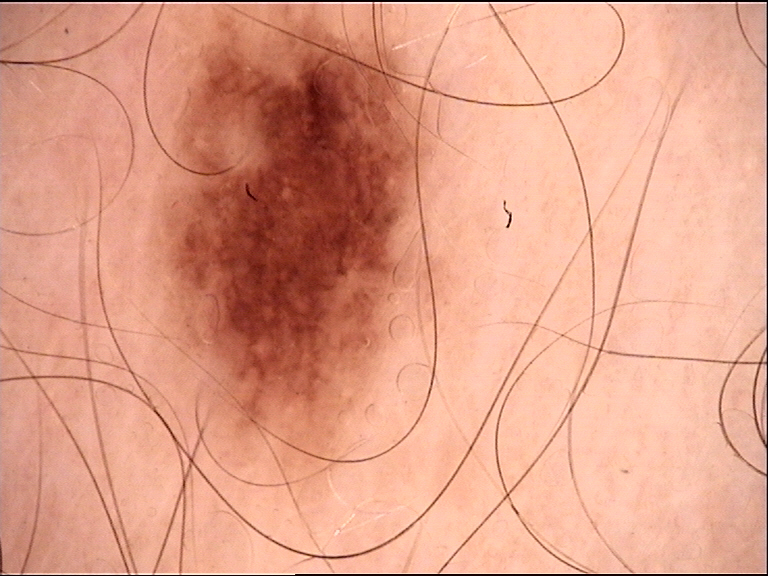label = junctional nevus (expert consensus).